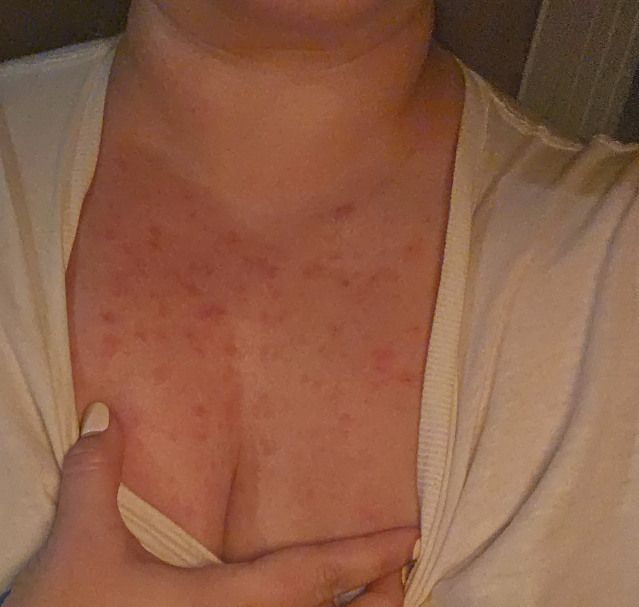assessment: unable to determine
shot_type: at a distance
skin_tone:
  fitzpatrick: III
  monk_skin_tone: 3
duration: less than one week
patient: female, age 30–39
symptoms:
  - bothersome appearance
  - enlargement
  - itching
texture: raised or bumpy
patient_category: a rash